The photograph was taken at an angle.
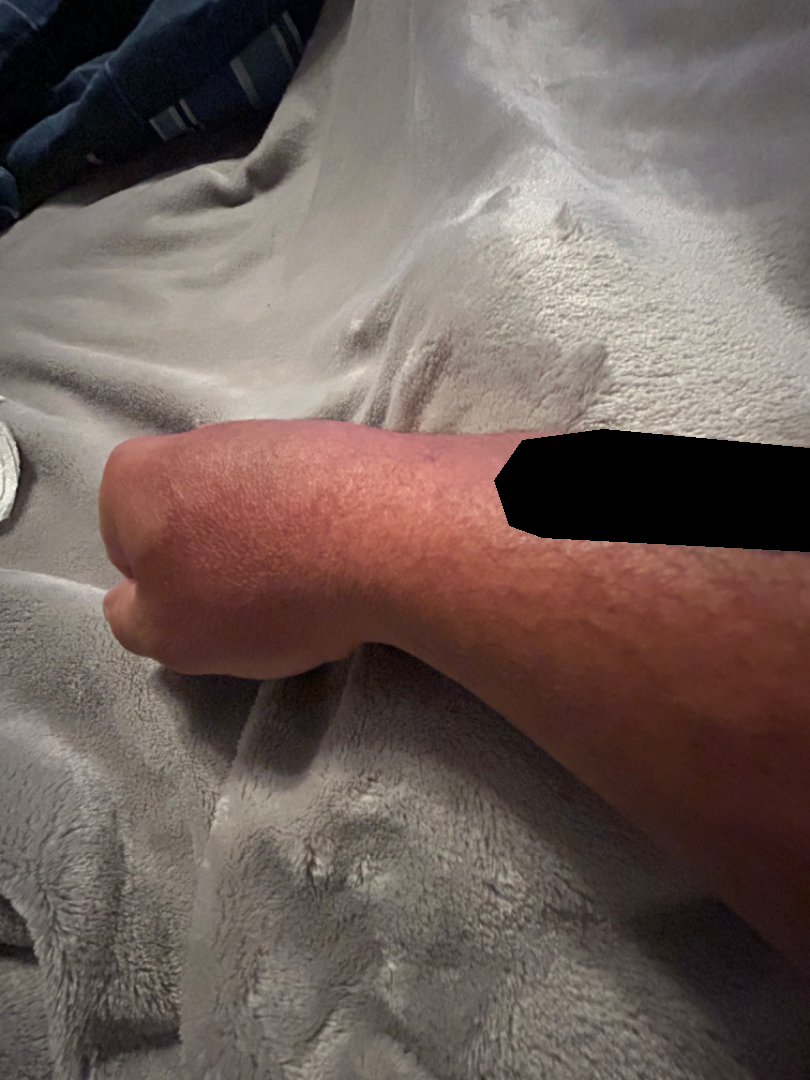<report>
  <skin_tone>
    <fitzpatrick>V</fitzpatrick>
    <monk_skin_tone>2</monk_skin_tone>
  </skin_tone>
  <differential>
    <Granuloma annulare>0.54</Granuloma annulare>
    <Tinea>0.23</Tinea>
    <Eczema>0.23</Eczema>
  </differential>
</report>